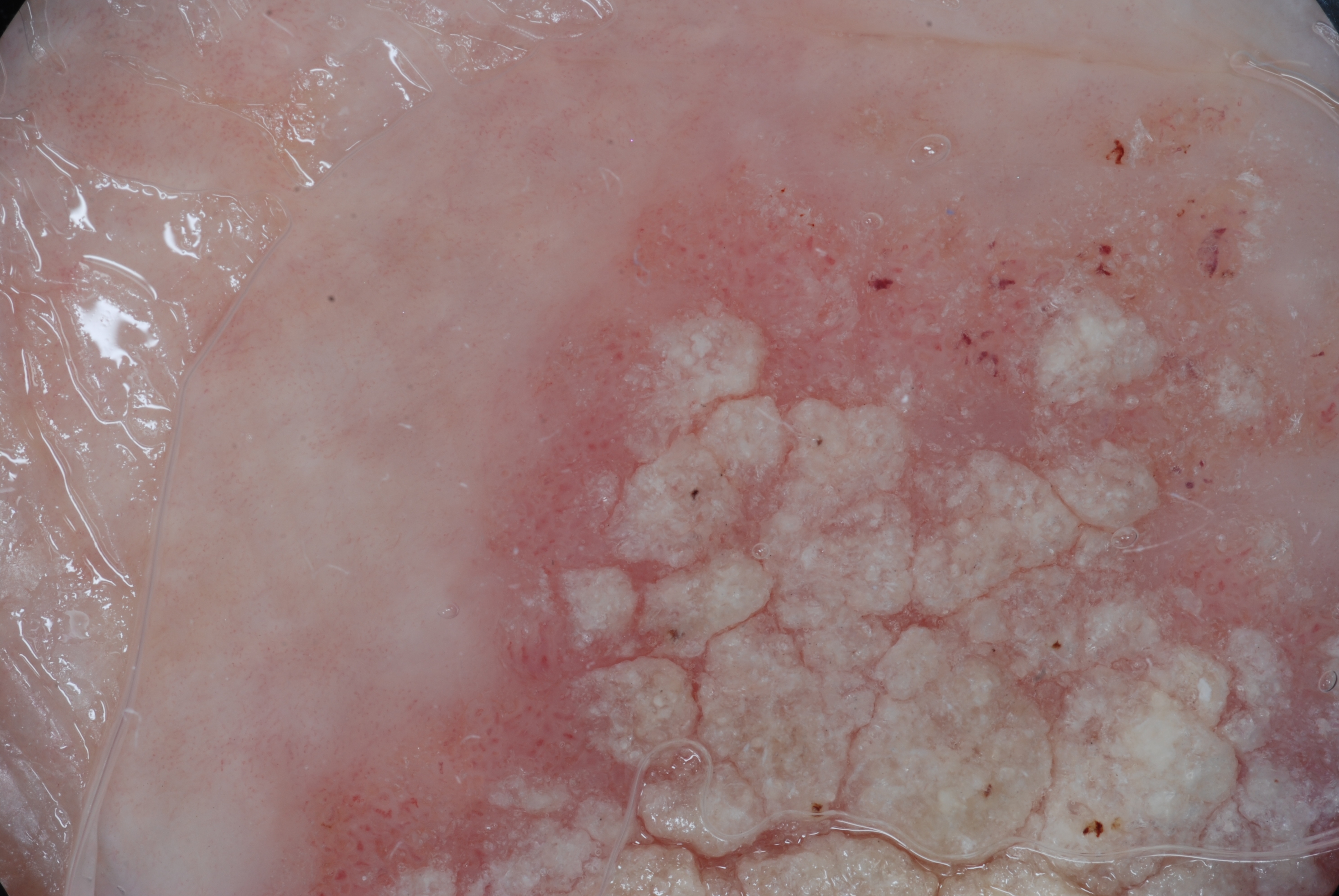patient: female, aged 83 or older | modality: dermoscopy | absent dermoscopic features: streaks, milia-like cysts, pigment network, and negative network | lesion location: [255,12,1332,893] | size: large | diagnostic label: a seborrheic keratosis, a benign skin lesion.